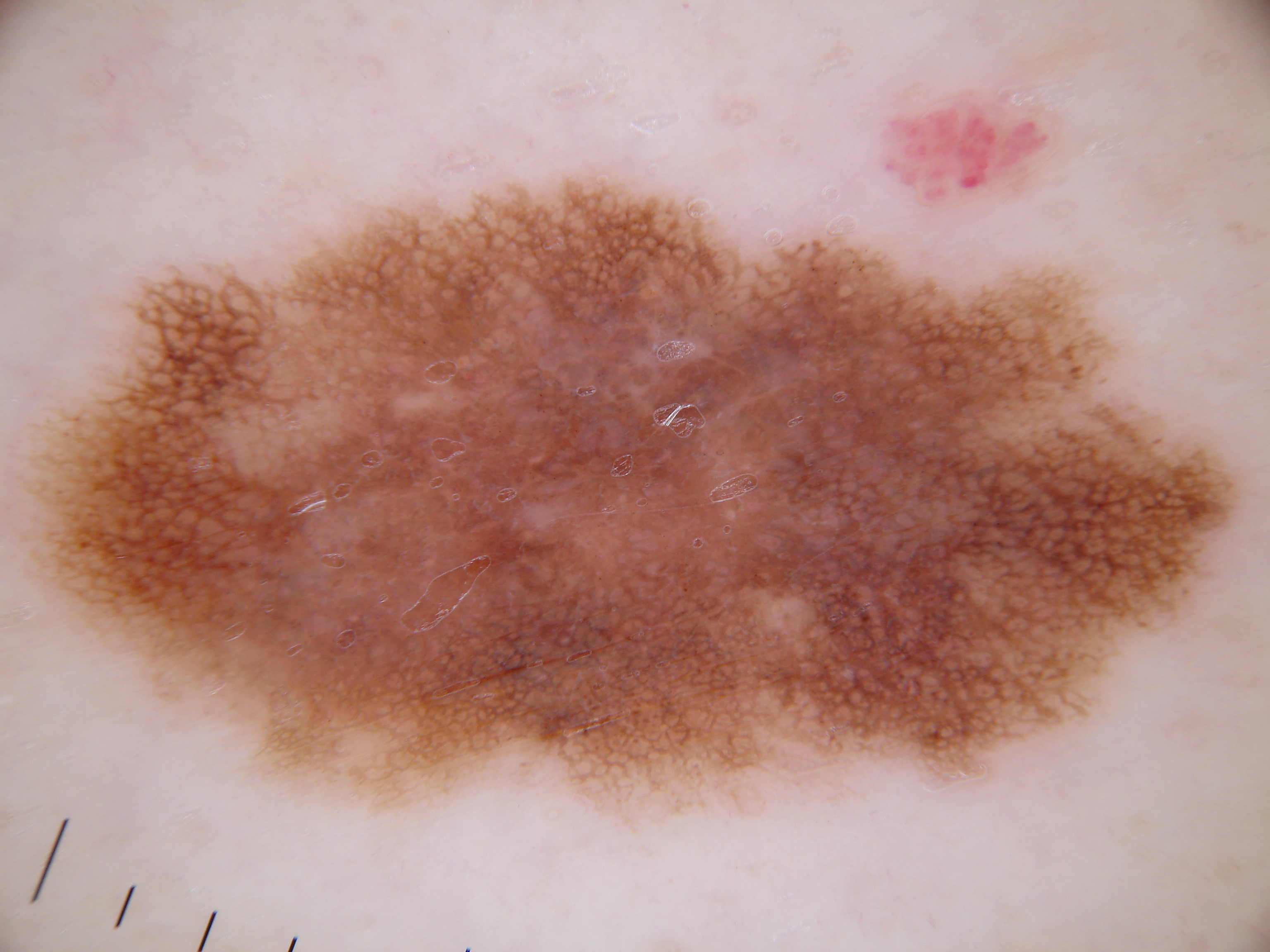imaging=dermoscopy | extent=large | dermoscopic features=pigment network | bounding box=<bbox>5, 157, 1248, 842</bbox> | assessment=a melanoma.